A dermoscopy image of a single skin lesion · a female patient approximately 35 years of age: 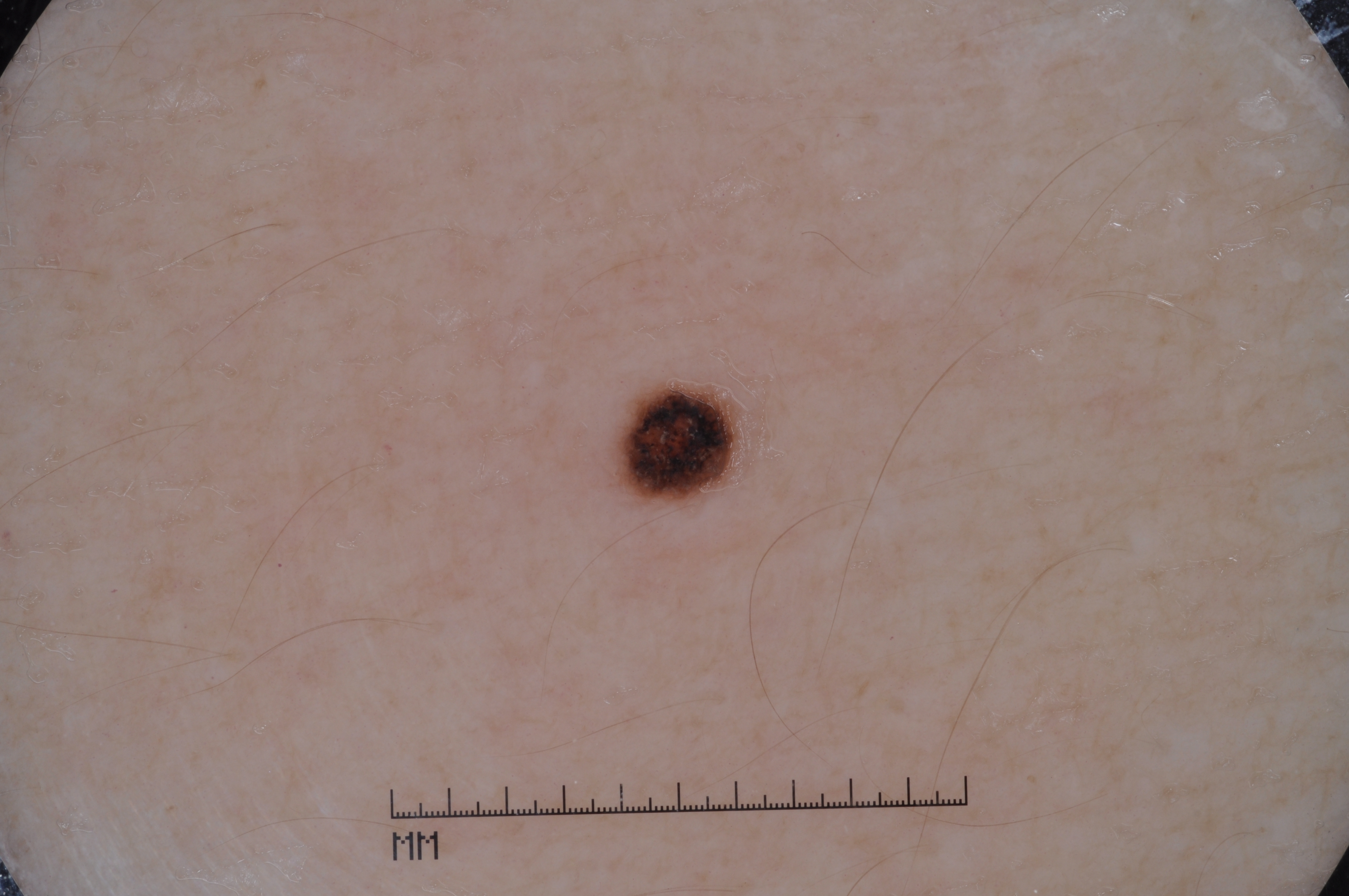Findings:
* bounding box — [589, 375, 766, 513]
* dermoscopic features assessed but absent — streaks, milia-like cysts, negative network, and pigment network
* diagnosis — a melanocytic nevus